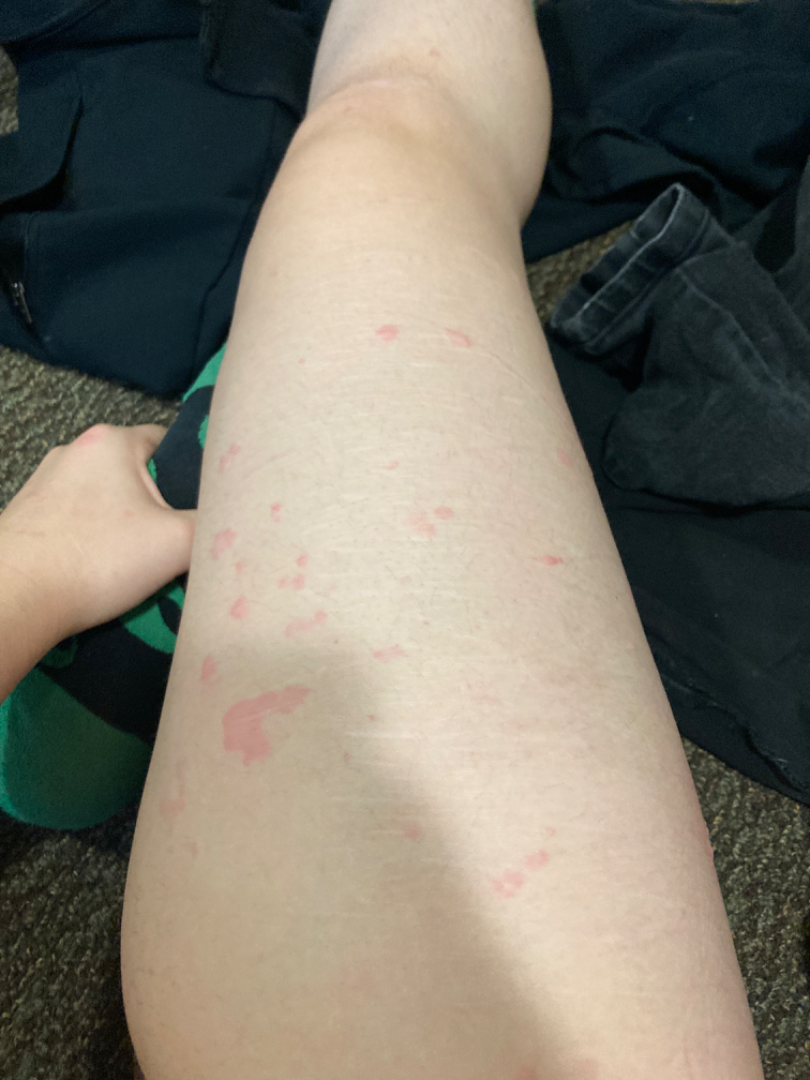Patient information: An image taken at a distance. Review: On photographic review by a dermatologist: most likely Urticaria; also on the differential is Eczema.